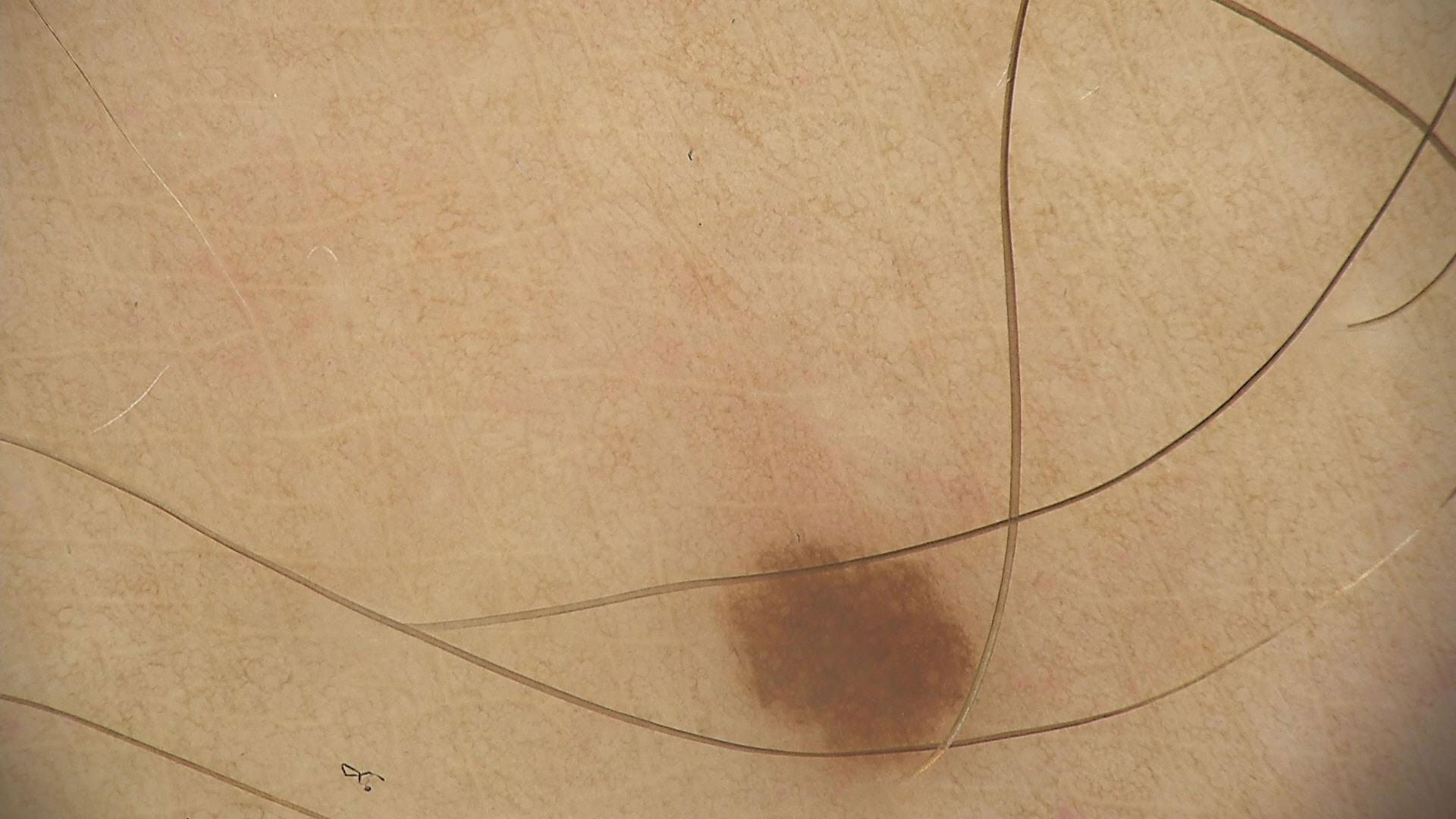Classified as a junctional nevus.